The patient is 40–49, female. The lesion involves the leg. A close-up photograph — 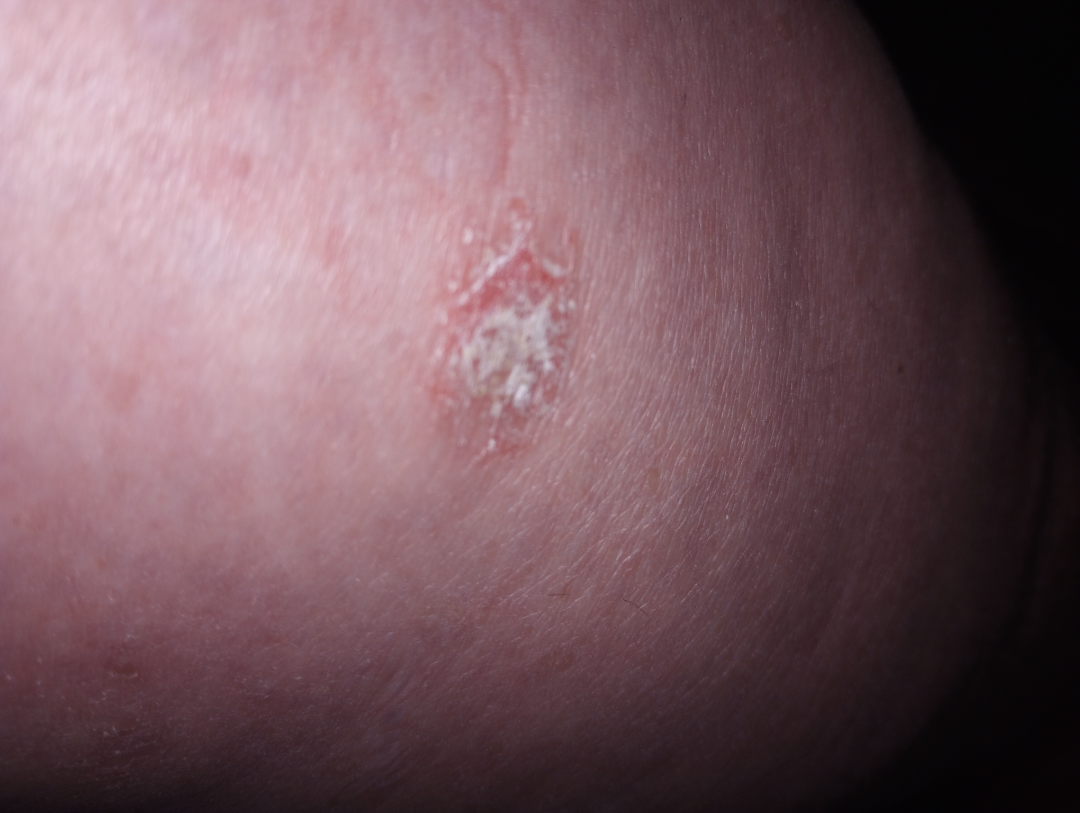Review:
The reviewer was unable to grade this case for skin condition.